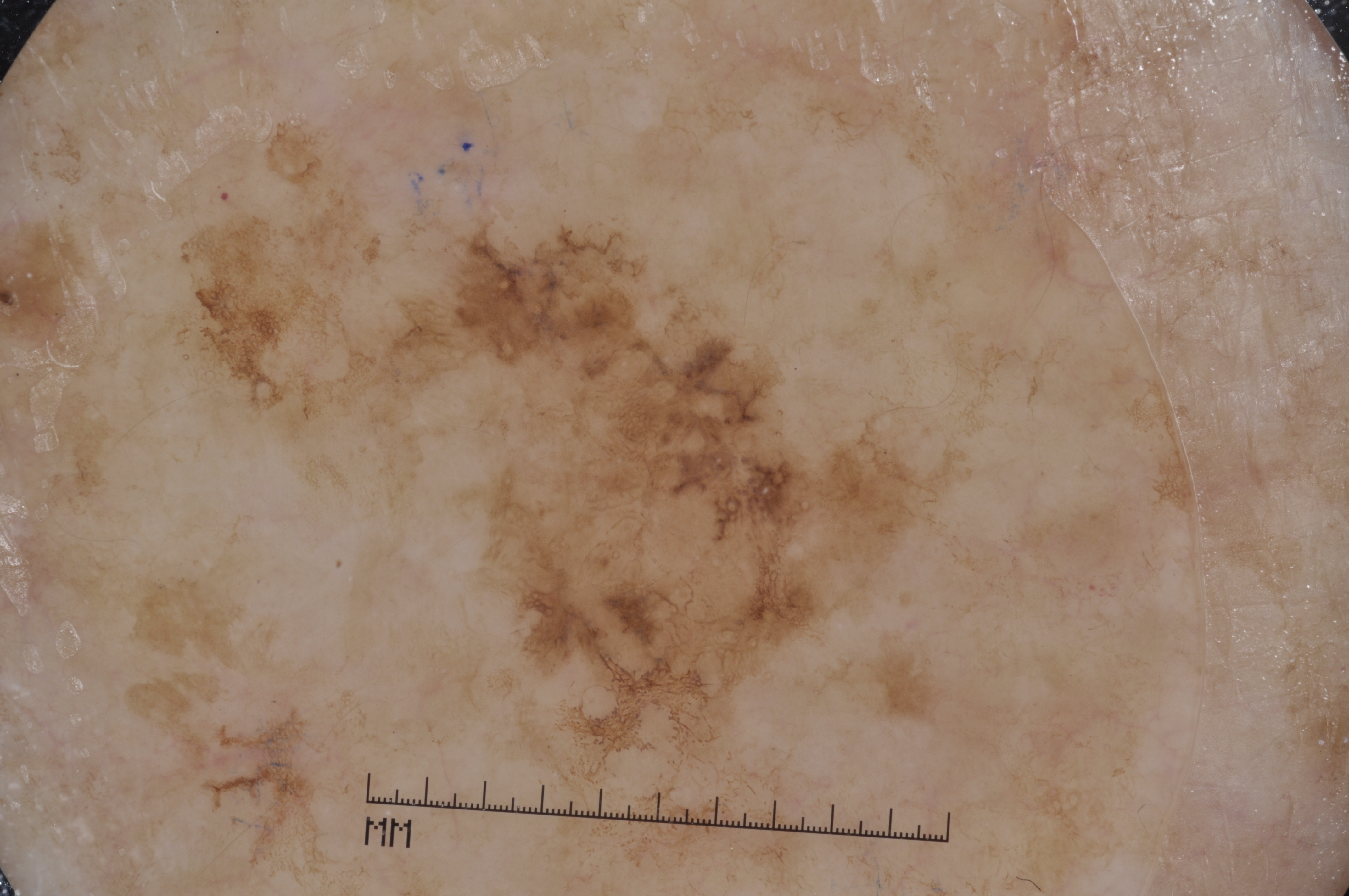{
  "image": {
    "modality": "dermoscopy"
  },
  "patient": {
    "sex": "male",
    "age_approx": 80
  },
  "dermoscopic_features": {
    "present": [
      "milia-like cysts",
      "pigment network"
    ],
    "absent": [
      "negative network",
      "streaks"
    ]
  },
  "lesion_location": {
    "bbox_xyxy": [
      161,
      117,
      974,
      883
    ]
  },
  "diagnosis": {
    "name": "melanoma",
    "malignancy": "malignant",
    "lineage": "melanocytic",
    "provenance": "histopathology"
  }
}